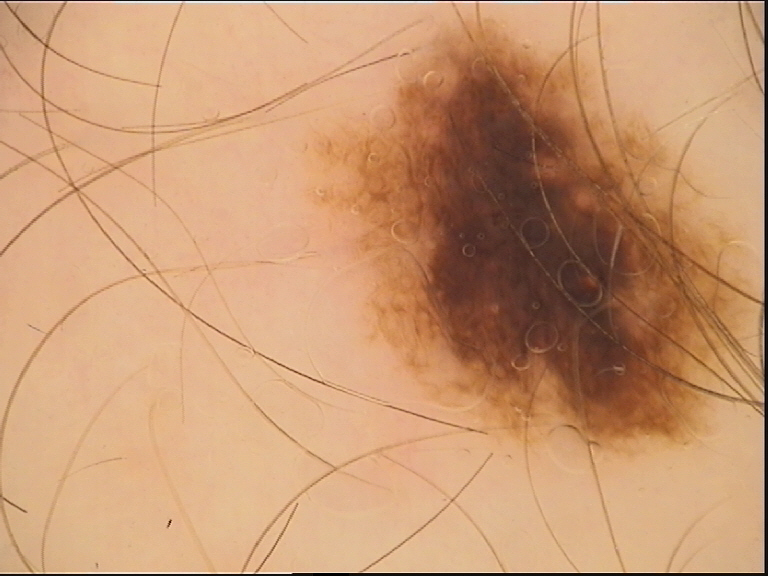Impression:
Diagnosed as a benign lesion — a dysplastic compound nevus.